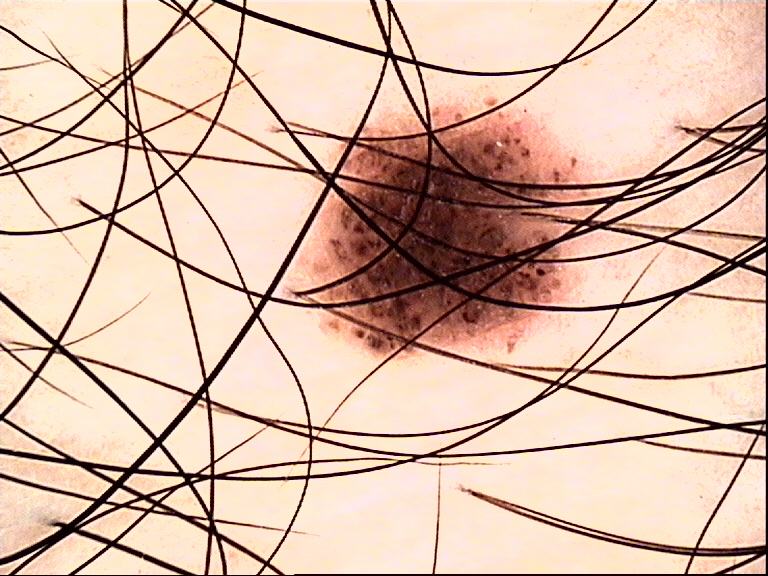Q: What is this lesion?
A: dysplastic junctional nevus (expert consensus)